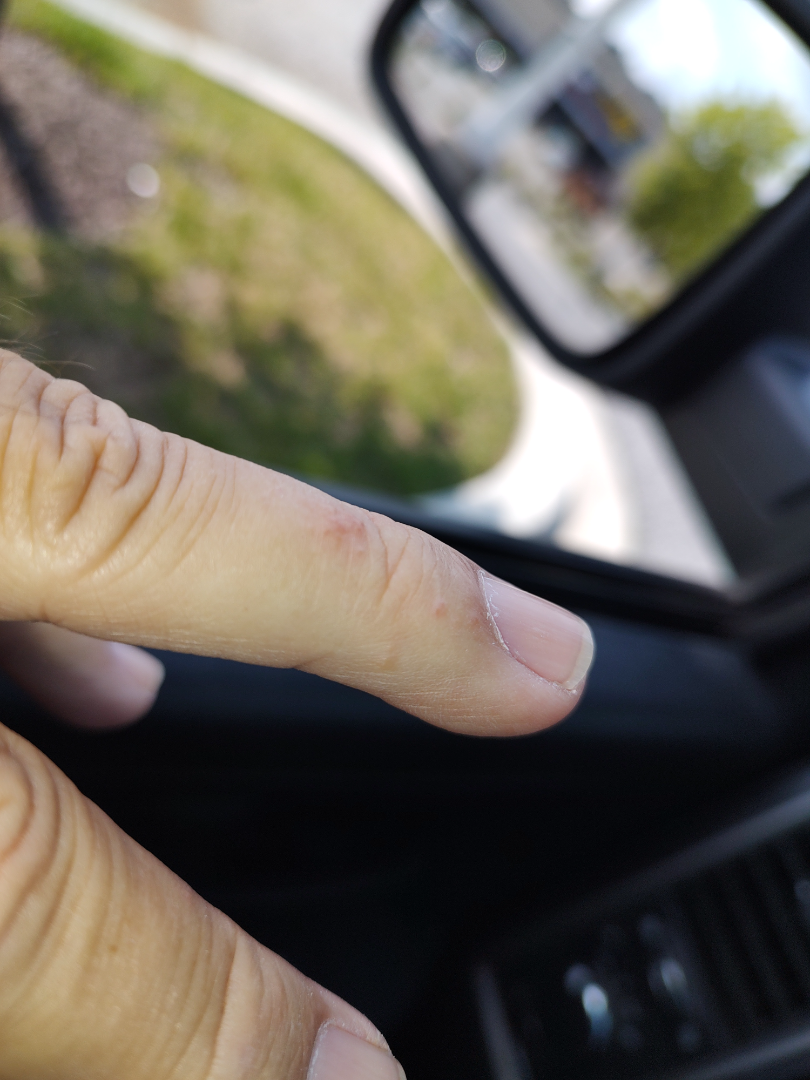assessment=could not be assessed | self-categorized as=a rash | present for=less than one week | reported symptoms=itching | subject=male, age 60–69 | surface texture=raised or bumpy and fluid-filled | shot type=at an angle.